A skin lesion imaged with a dermatoscope · the patient is a male in their mid-40s:
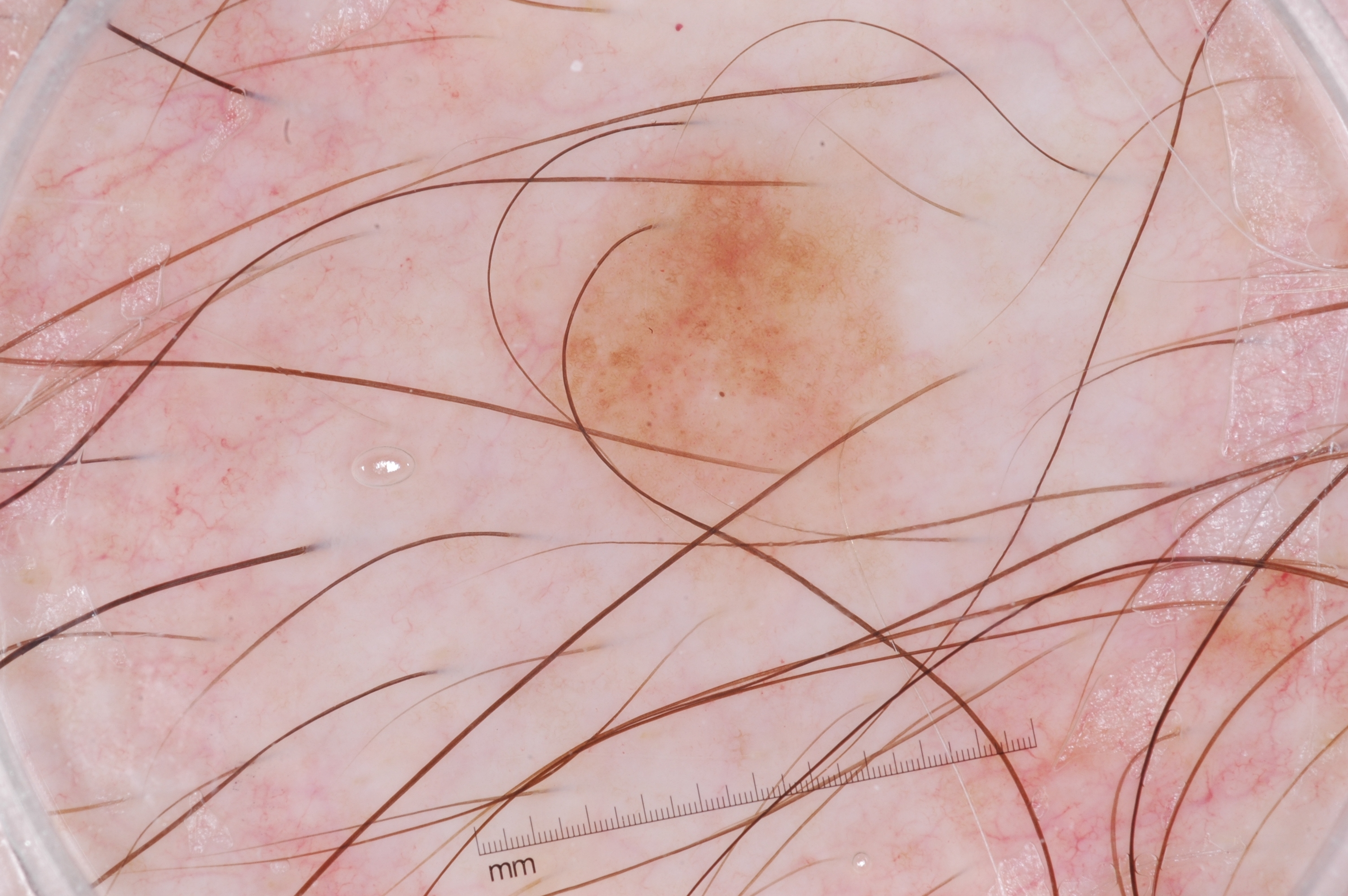Summary:
In (x1, y1, x2, y2) order, the lesion is located at bbox=[527, 154, 906, 497]. On dermoscopy, the lesion shows pigment network and milia-like cysts.
Conclusion:
The lesion was assessed as a melanocytic nevus.